A dermoscopic image of a skin lesion:
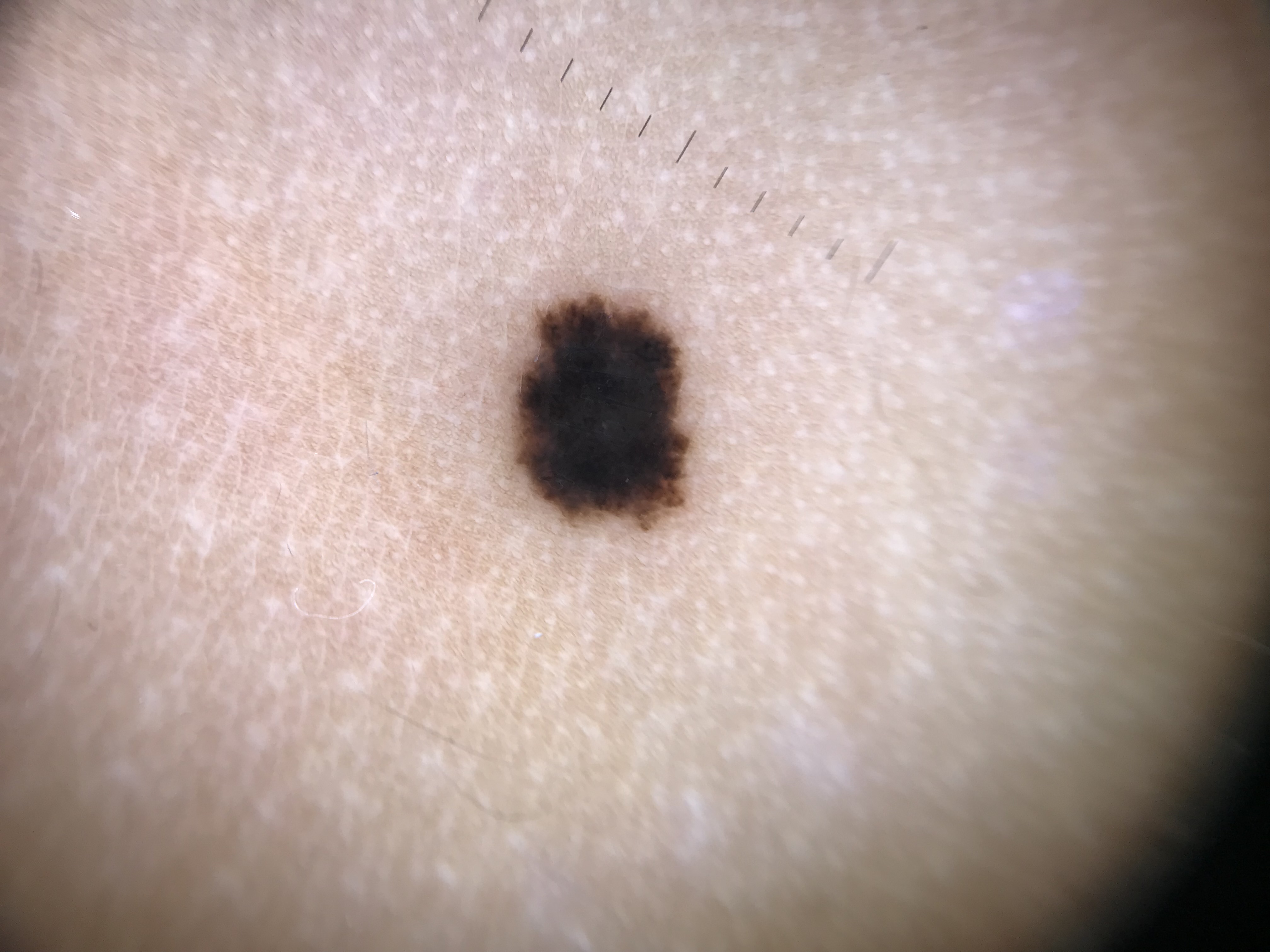  diagnosis:
    name: Spitz/Reed nevus
    code: srjd
    malignancy: benign
    super_class: melanocytic
    confirmation: expert consensus